The contributor is 50–59, female; the head or neck is involved; this image was taken at an angle: 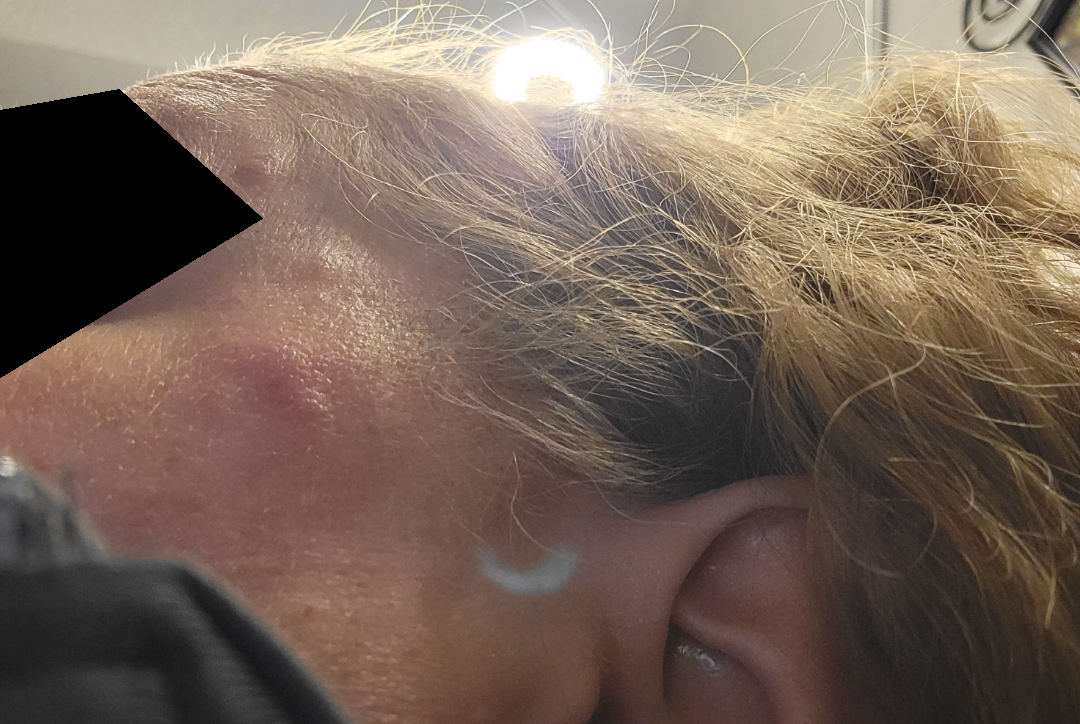Reported lesion symptoms include pain, enlargement, itching and burning.
The patient described the issue as a rash.
Rosacea, Allergic Contact Dermatitis and Cutaneous lupus were considered with similar weight.